A dermoscopy image of a single skin lesion.
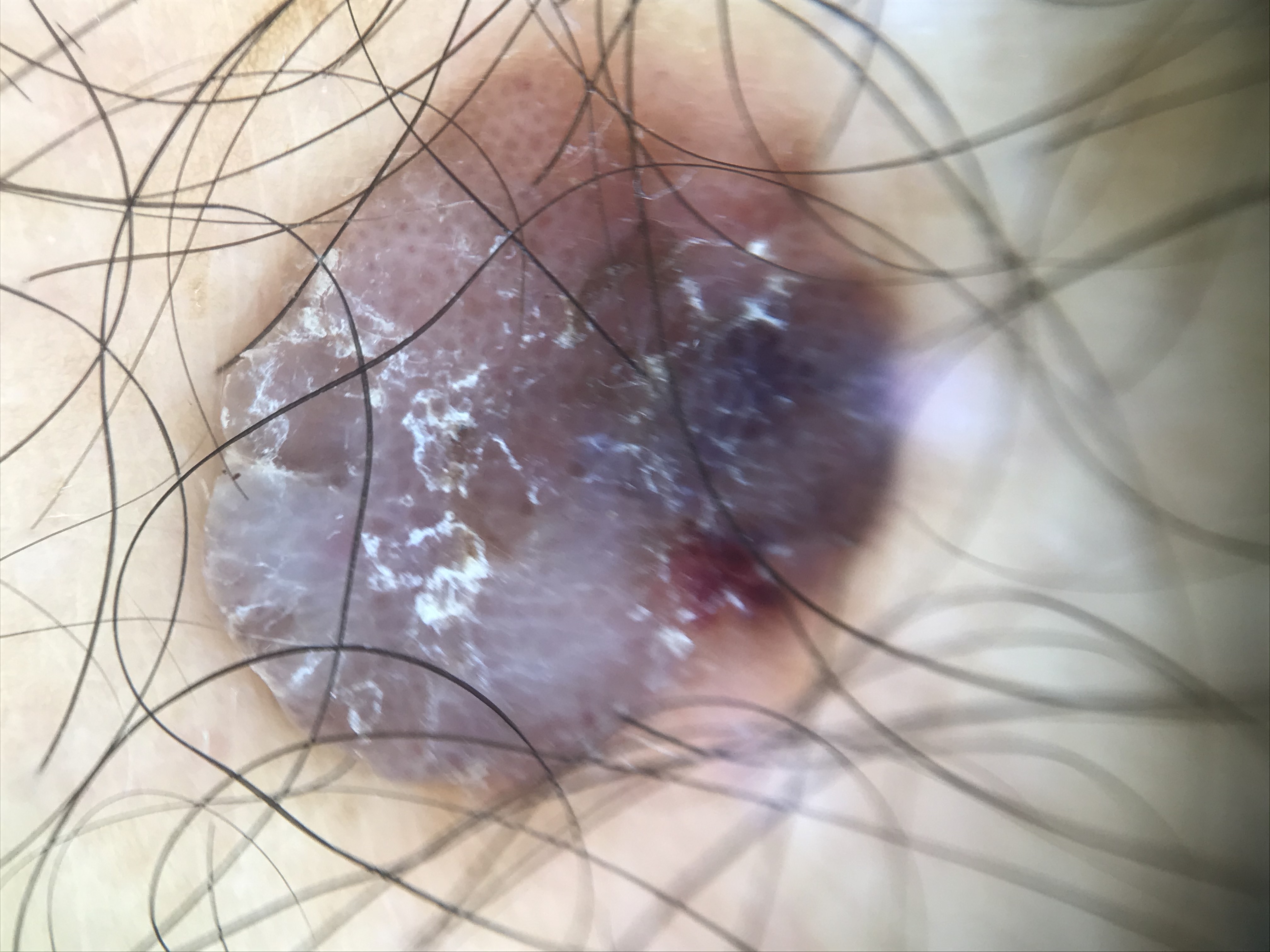Impression:
Consistent with a keratinocytic lesion — a seborrheic keratosis.